This is a close-up image; the lesion involves the top or side of the foot.
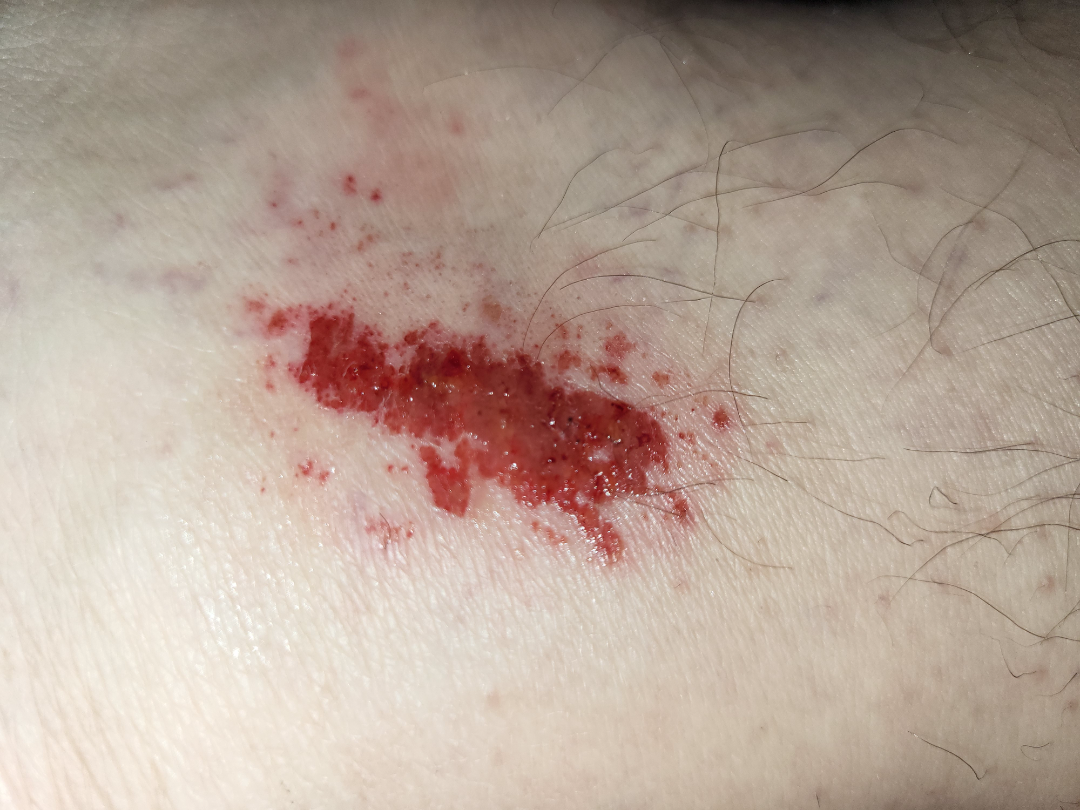No relevant systemic symptoms.
The patient considered this a rash.
Present for about one day.
On teledermatology review, favoring Superficial wound of body region; also consider superficial hemorrhage; also on the differential is Blister.